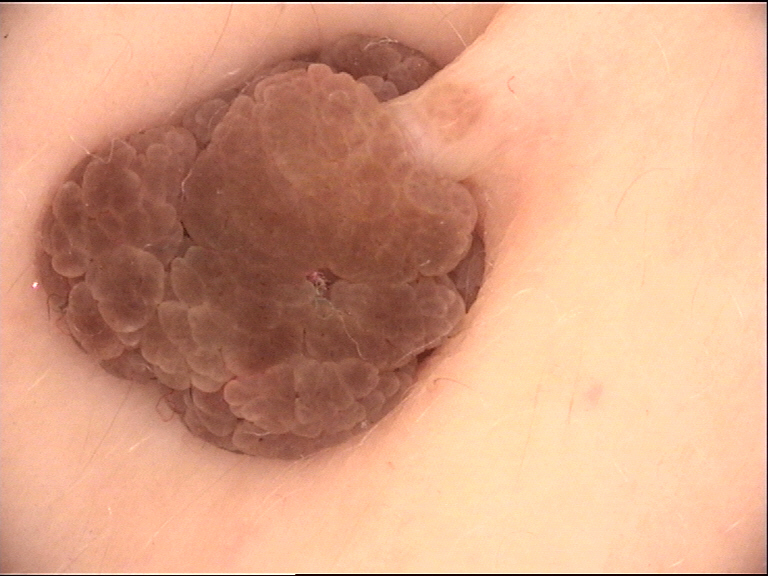assessment=dermal nevus (expert consensus)